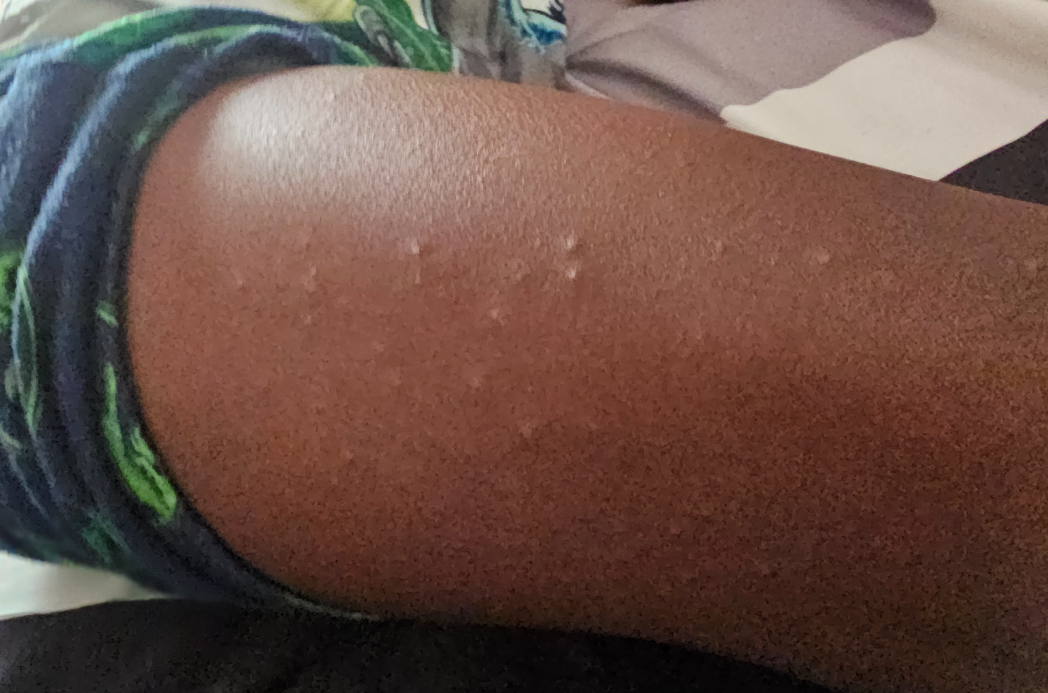The reviewing dermatologist's impression was: favoring Folliculitis.